Texture is reported as raised or bumpy; the condition has been present for one to four weeks; the arm is involved; male subject, age 40–49; this image was taken at an angle; self-categorized by the patient as a rash; the contributor reports itching.
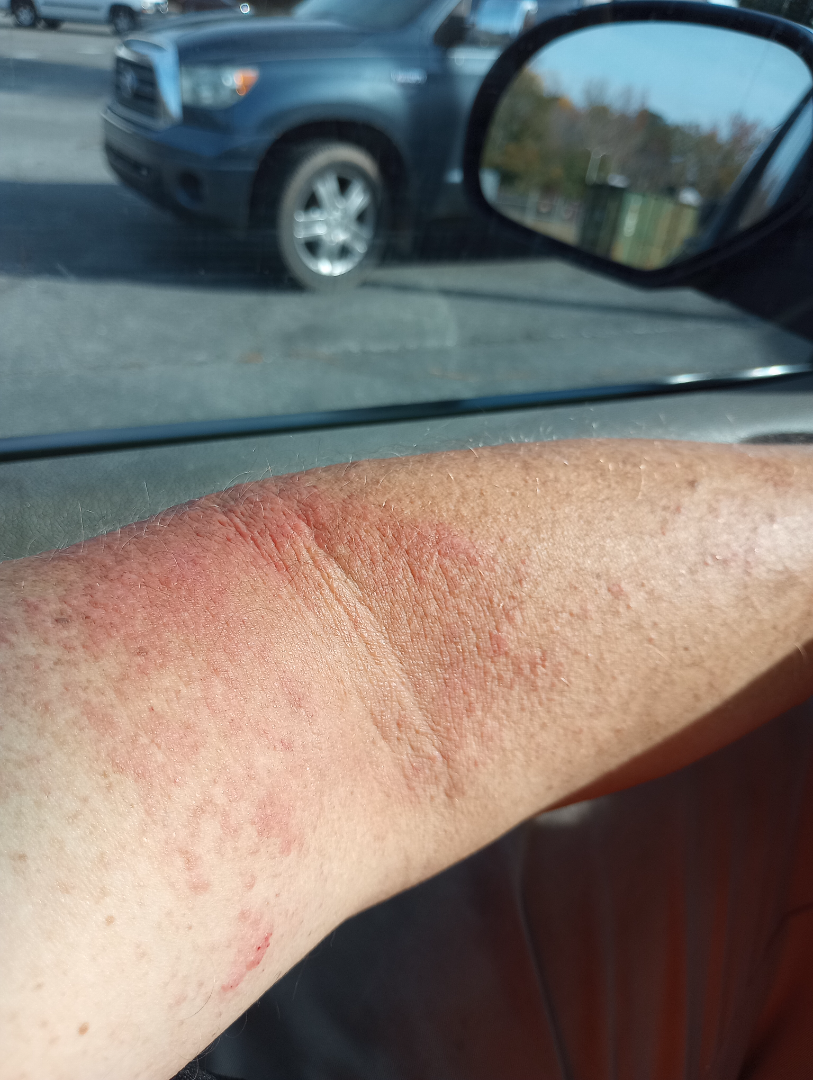On dermatologist assessment of the image: Eczema (leading); Psoriasis (considered); Allergic Contact Dermatitis (considered).